A dermatoscopic image of a skin lesion. A male patient, aged around 40:
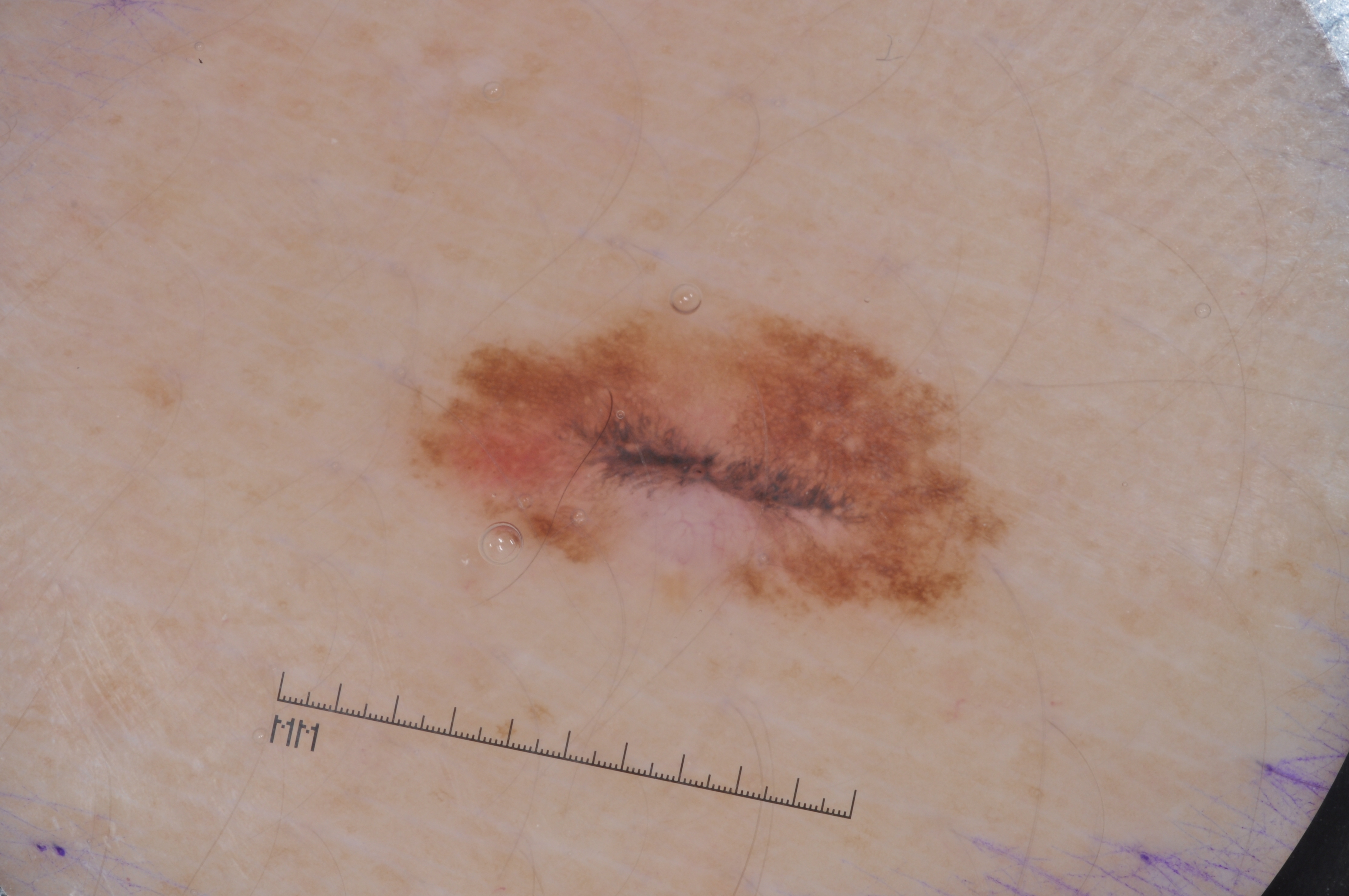dermoscopic features = negative network and pigment network; absent: milia-like cysts and streaks
lesion location = x1=390 y1=271 x2=1012 y2=643
impression = a melanocytic nevus